Female patient, age 30–39; the photo was captured at a distance; the lesion involves the top or side of the foot:
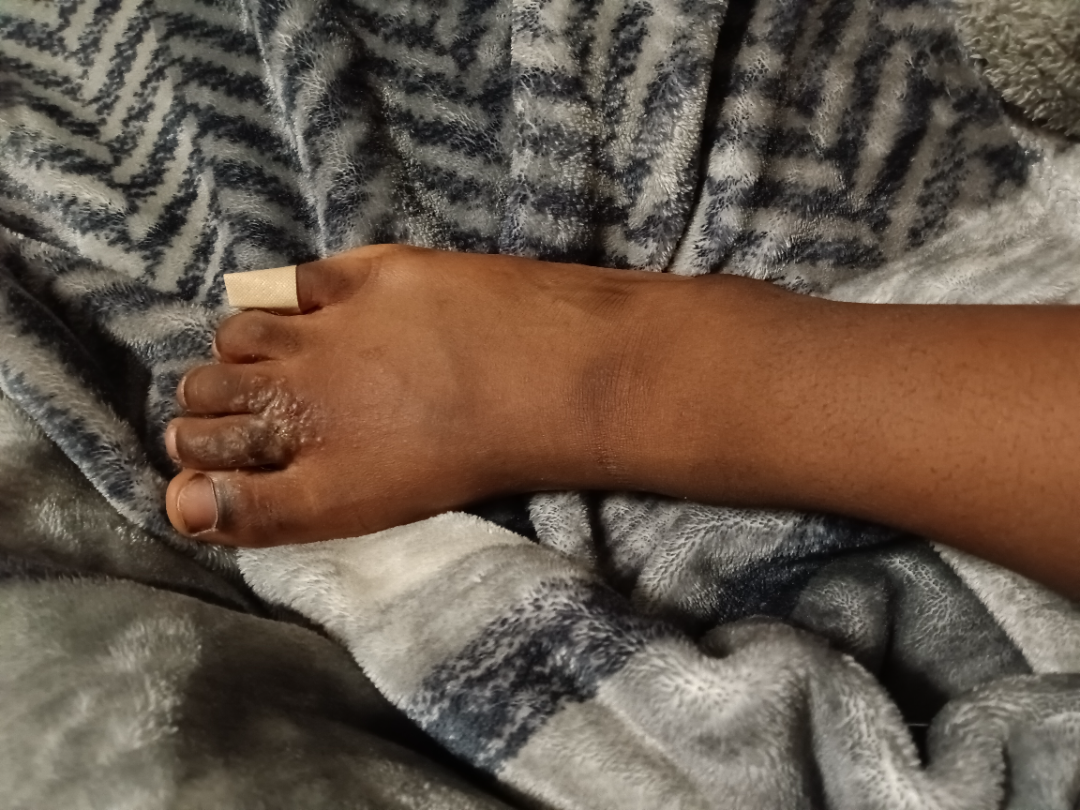Patient information:
The lesion is described as fluid-filled, flat and raised or bumpy. Reported duration is less than one week. The patient considered this a rash. No associated systemic symptoms reported.
Review:
On teledermatology review, the impression was split between Tinea and Eczema; possibly Skin and soft tissue atypical mycobacterial infection; a more distant consideration is Allergic Contact Dermatitis.